A dermoscopy image of a single skin lesion.
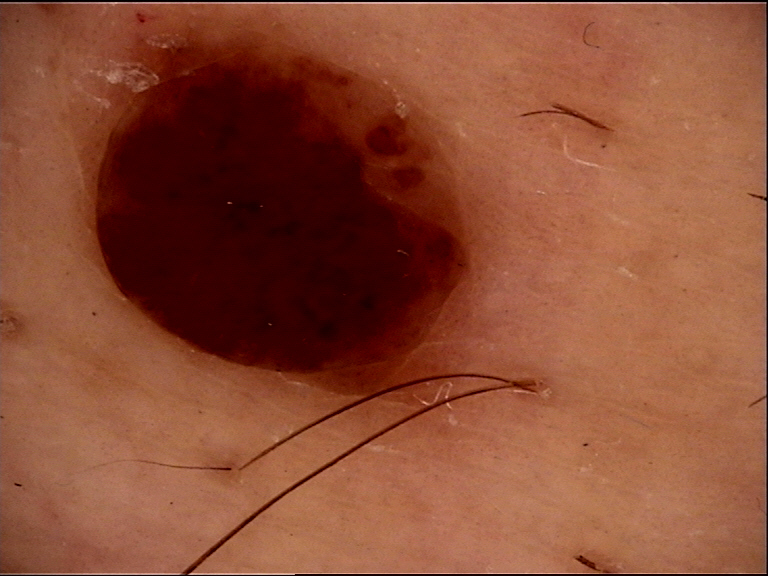The diagnostic label was a dermal nevus.